A dermoscopy image of a single skin lesion:
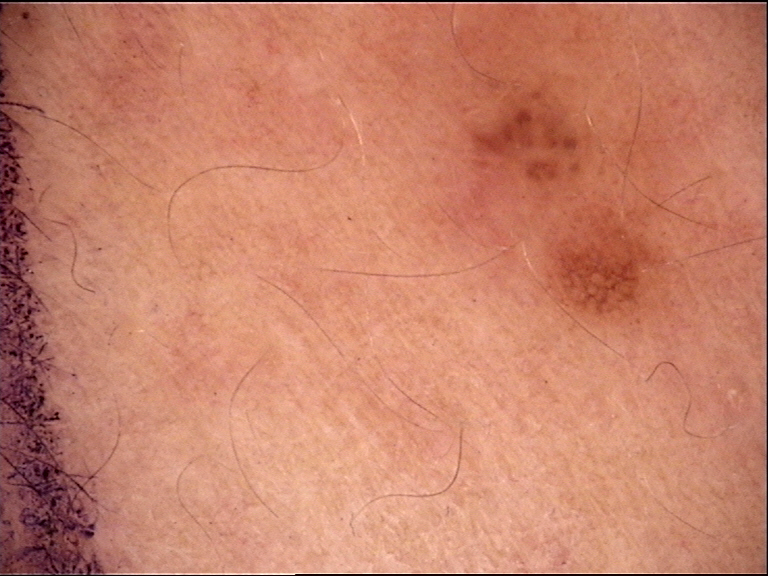Impression: Classified as a dysplastic junctional nevus.